The lesion involves the head or neck · the patient is 40–49, female · the photo was captured at an angle: 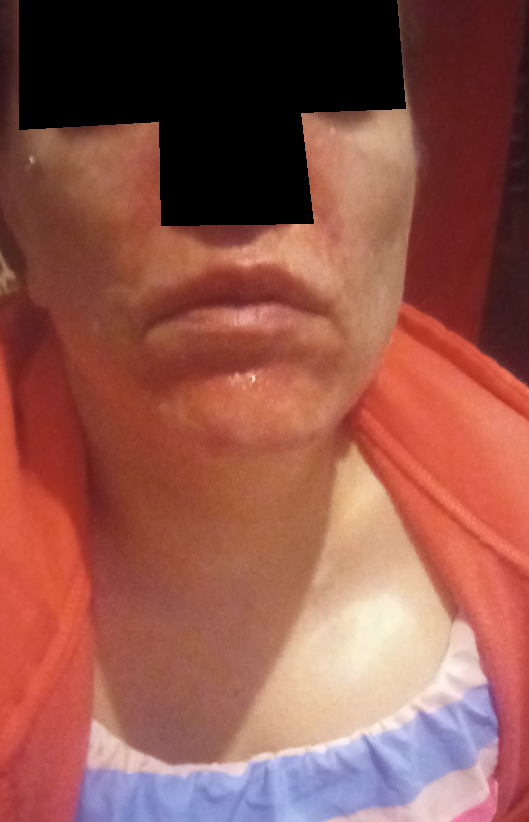The reviewing dermatologist was unable to assign a differential diagnosis from the image.